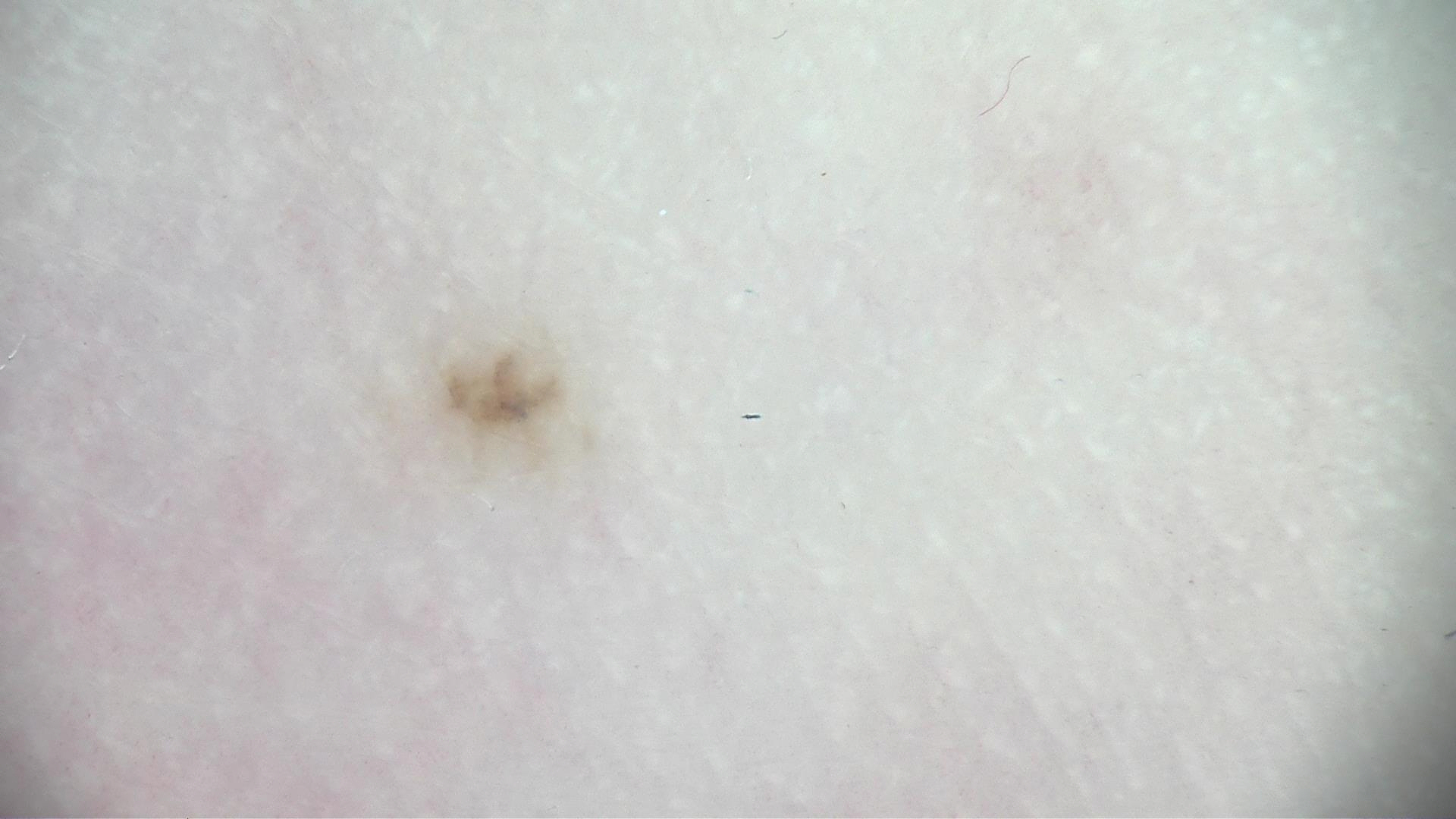The diagnostic label was an acral dysplastic junctional nevus.